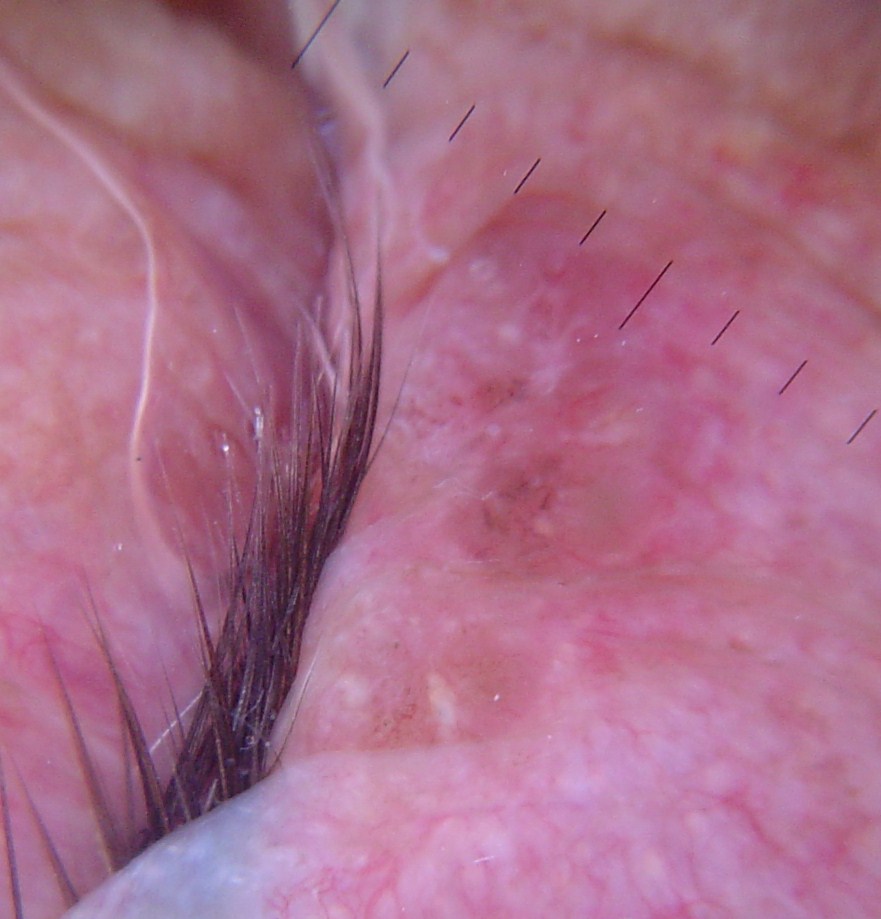A dermoscopy image of a single skin lesion. The morphology is that of a keratinocytic lesion. Histopathology confirmed a basal cell carcinoma.